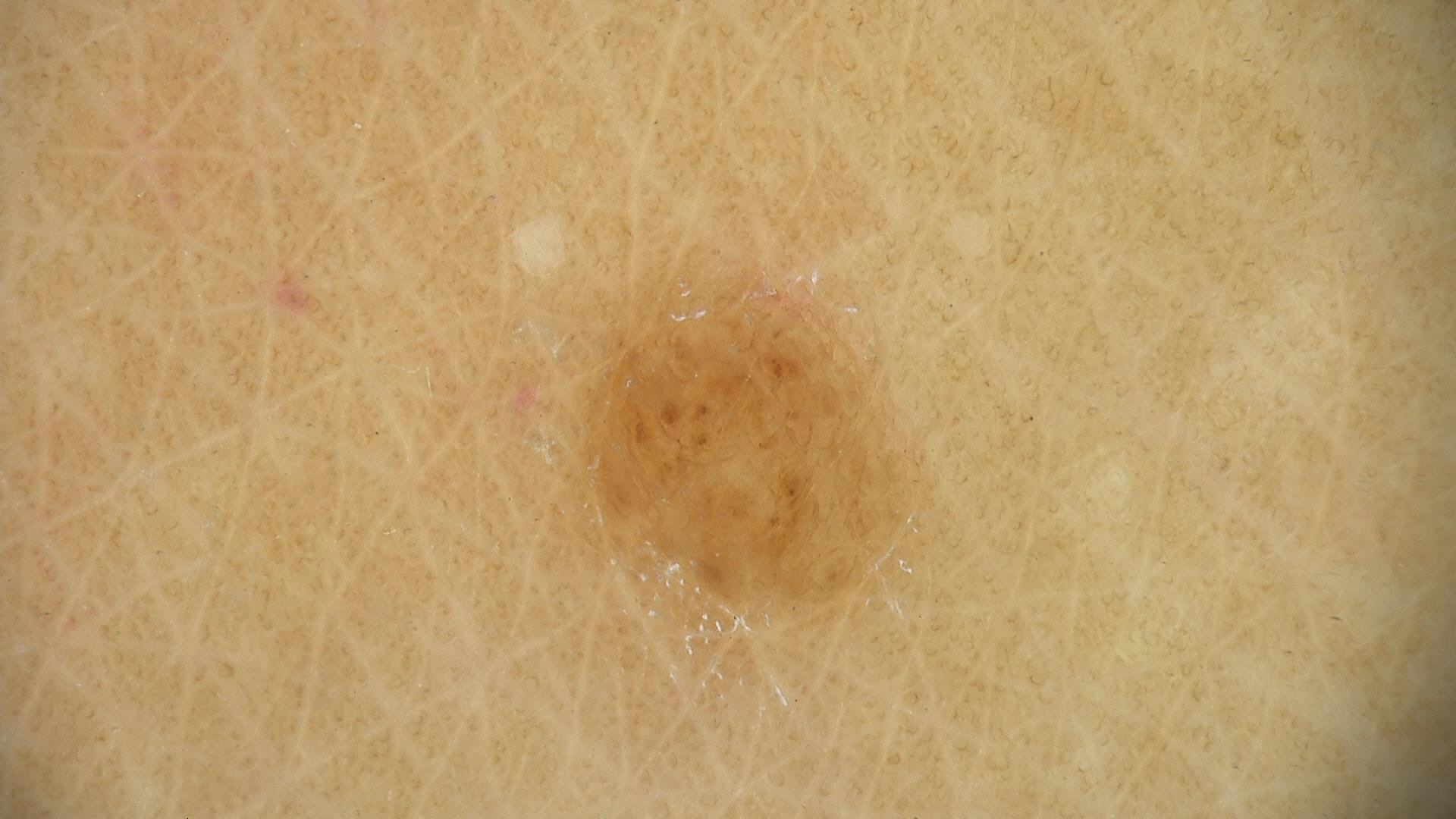The diagnostic label was a dermal nevus.